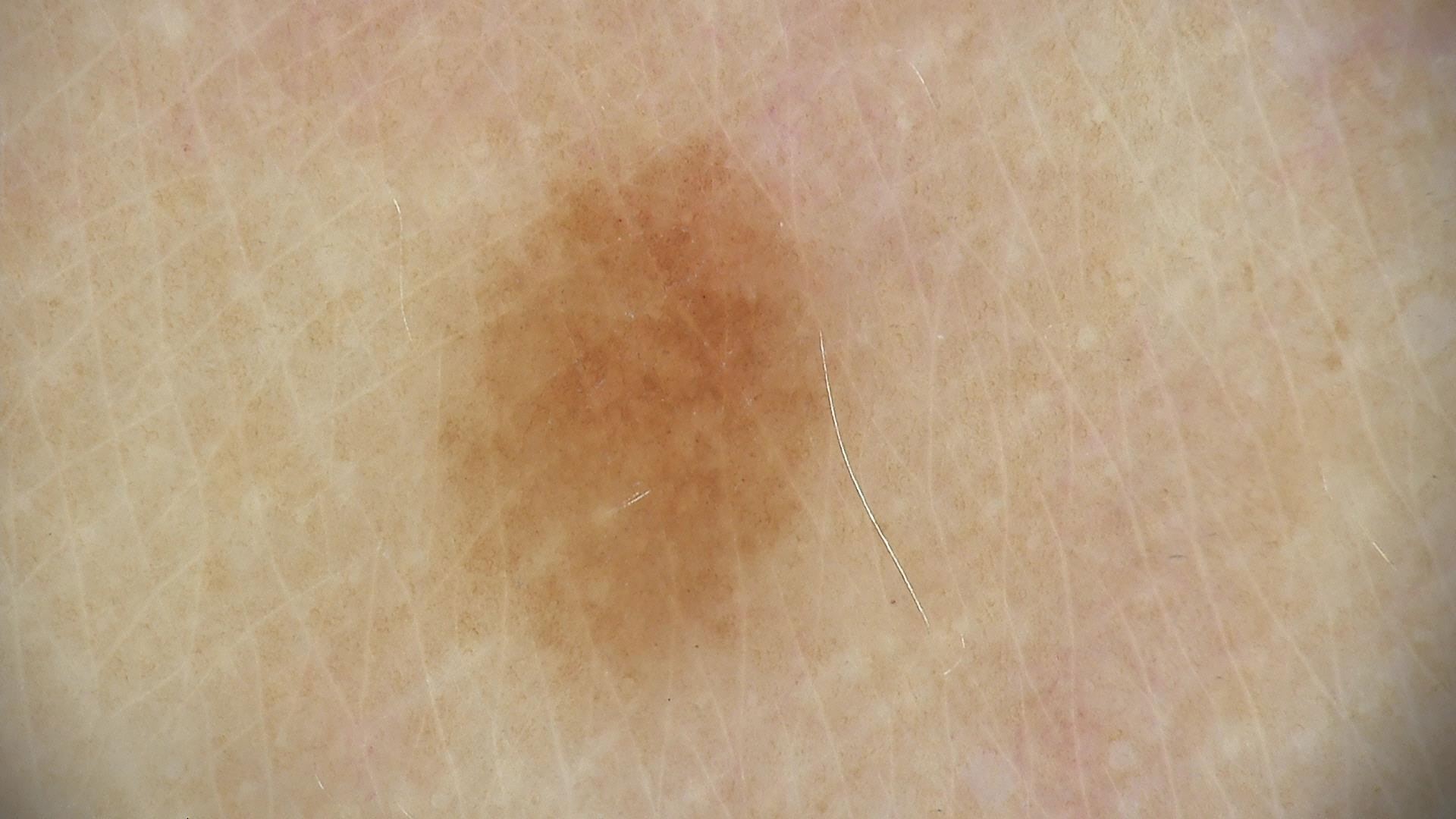A dermatoscopic image of a skin lesion. The morphology is that of a banal lesion. The diagnostic label was a junctional nevus.